Dermoscopy of a skin lesion.
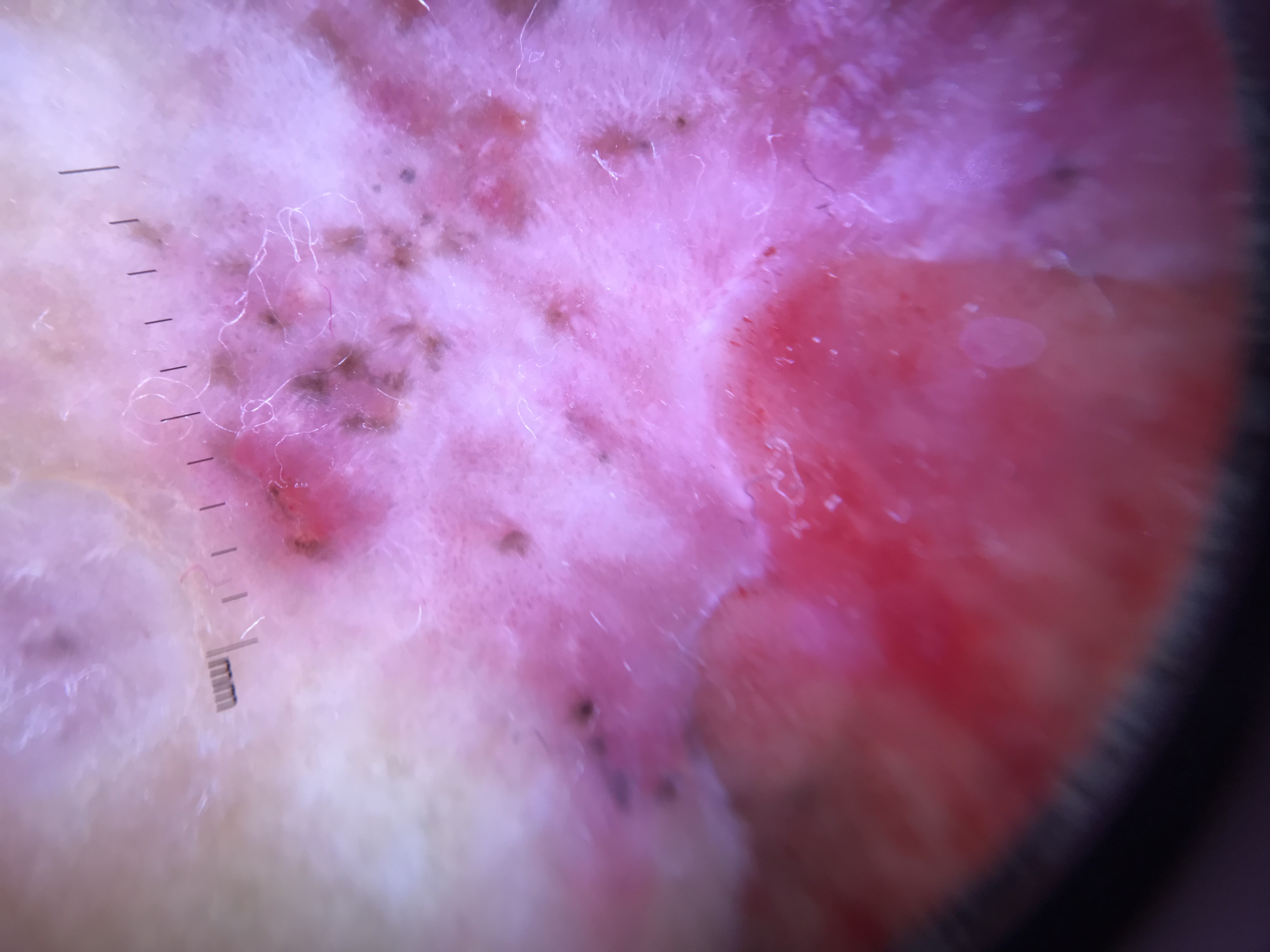Histopathology confirmed a keratinocytic lesion — a basal cell carcinoma.